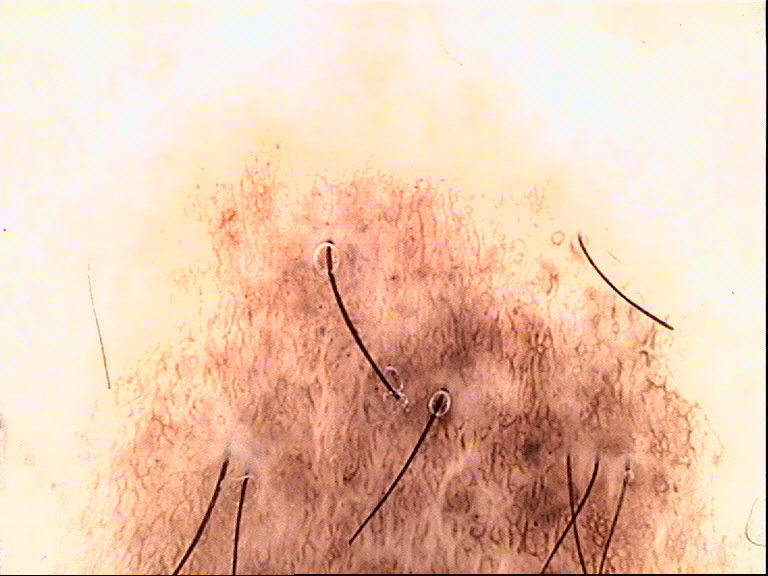class: congenital compound nevus (expert consensus).